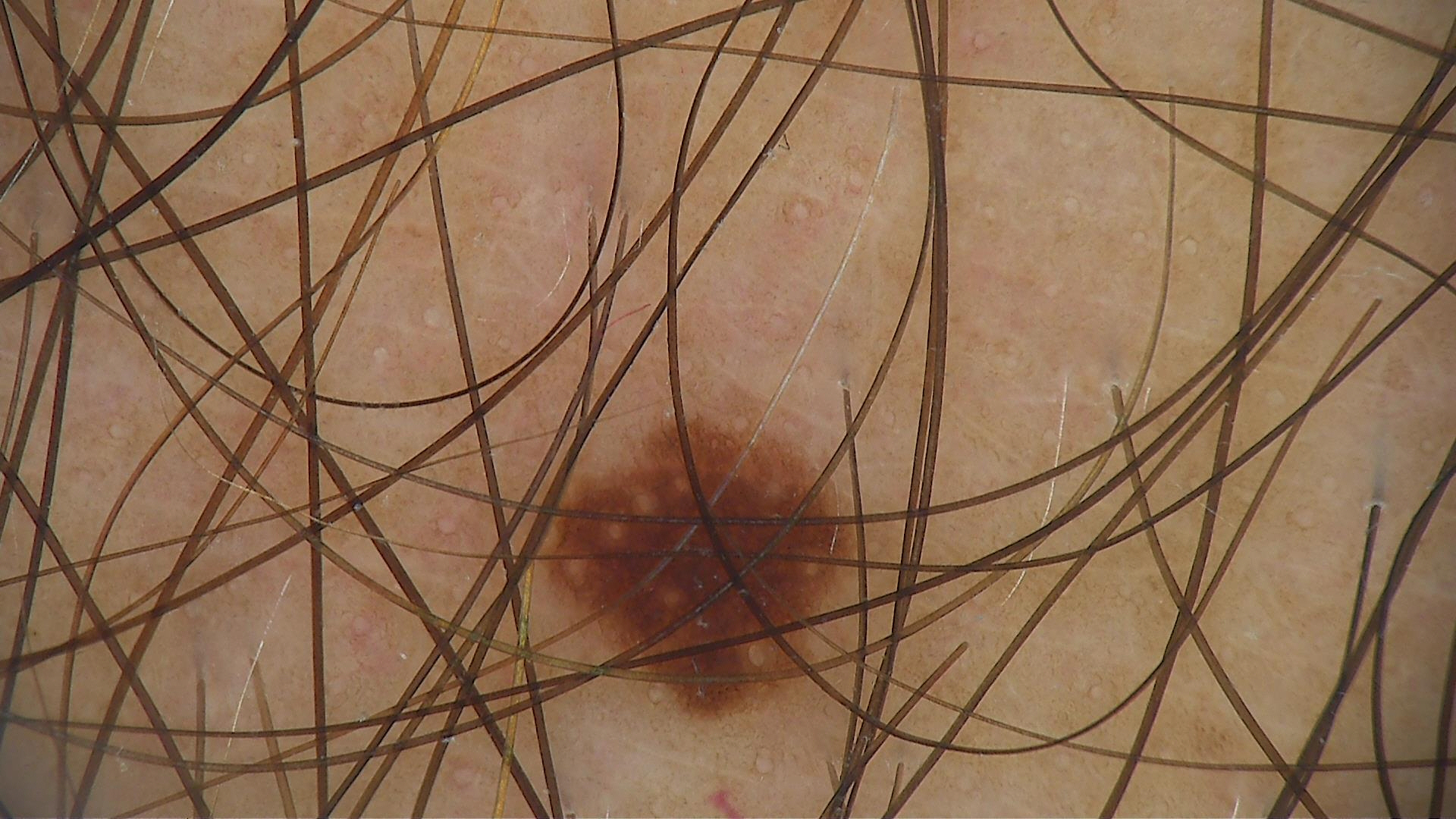Impression:
Labeled as a dysplastic junctional nevus.